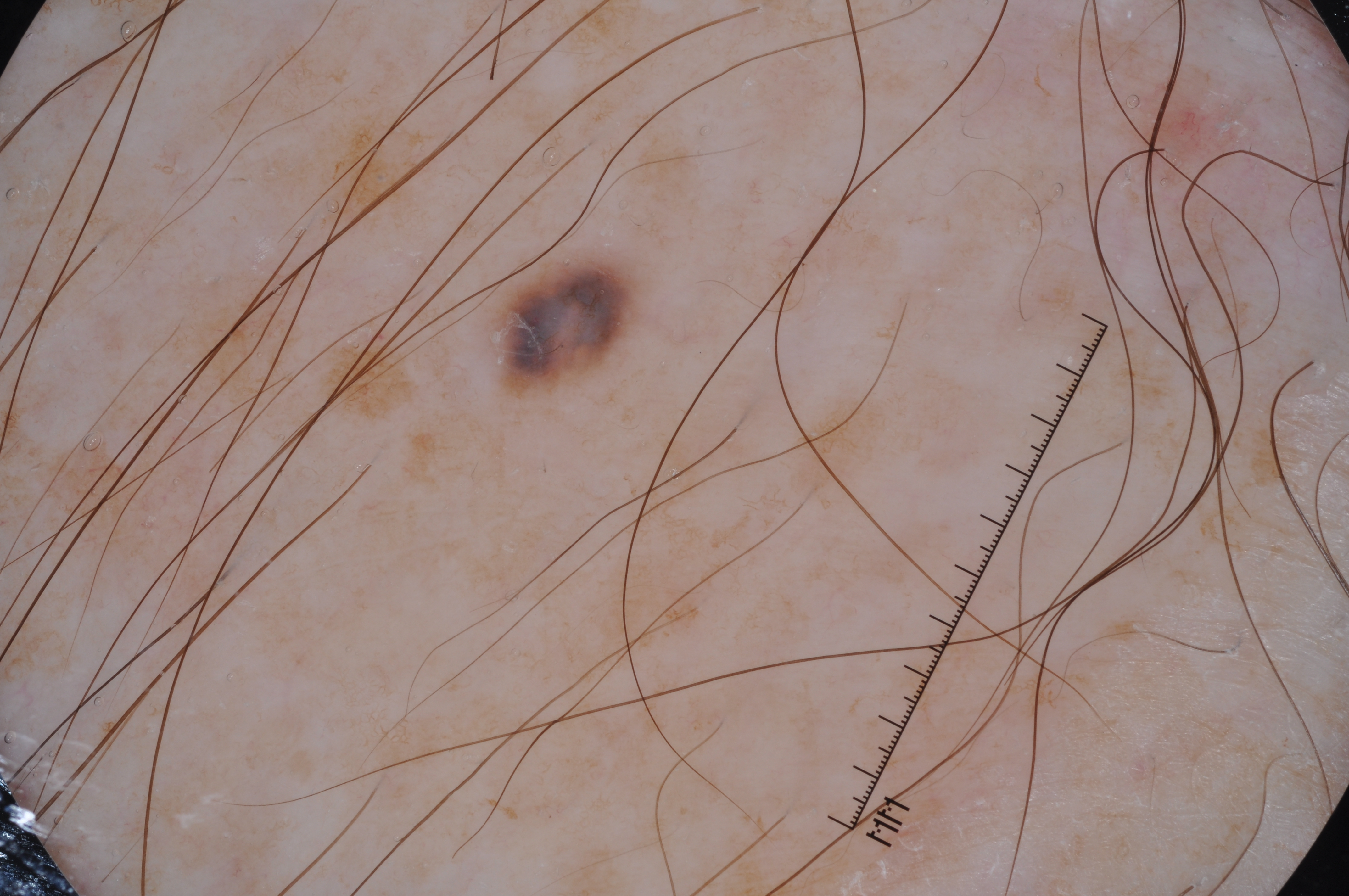Dermoscopy of a skin lesion.
A male patient aged 78-82.
Dermoscopic examination shows pigment network; no negative network, milia-like cysts, or streaks.
The lesion is bounded by left=481, top=242, right=647, bottom=402.
The lesion takes up about 2% of the image.
Expert review diagnosed this as a melanocytic nevus.